The patient is a female aged 18–29; the photograph was taken at an angle; located on the arm: 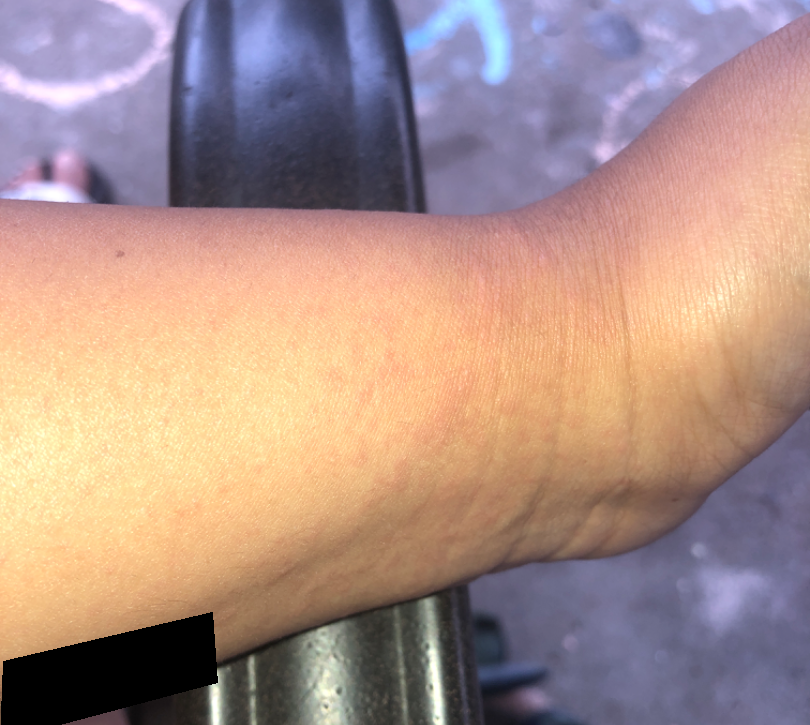History: The patient considered this a rash. Symptoms reported: itching and bothersome appearance. The patient notes the lesion is raised or bumpy. The patient notes the condition has been present for less than one week. Skin tone: Fitzpatrick phototype III. Impression: The differential, in no particular order, includes Acute dermatitis, NOS and Eczema; less probable is Drug Rash; less likely is Viral Exanthem; lower on the differential is Allergic Contact Dermatitis.